A female patient aged 64 · the referring clinician suspected basal cell carcinoma · a skin lesion imaged with a dermatoscope — 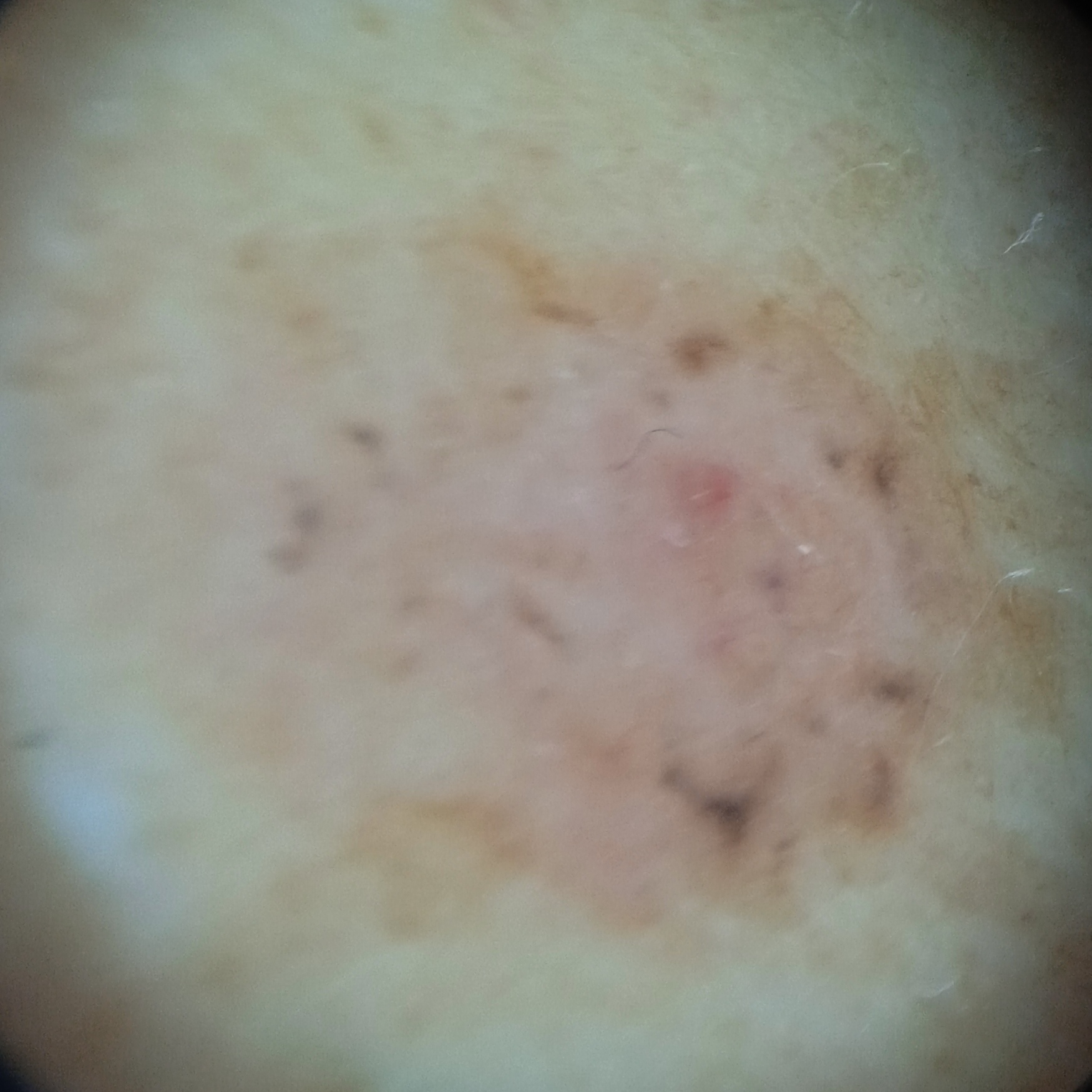{"lesion_size": {"diameter_mm": 9.8}, "diagnosis": {"name": "basal cell carcinoma", "malignancy": "malignant", "procedure": "excision", "tumor_thickness_mm": 1.0}}